A dermoscopy image of a single skin lesion.
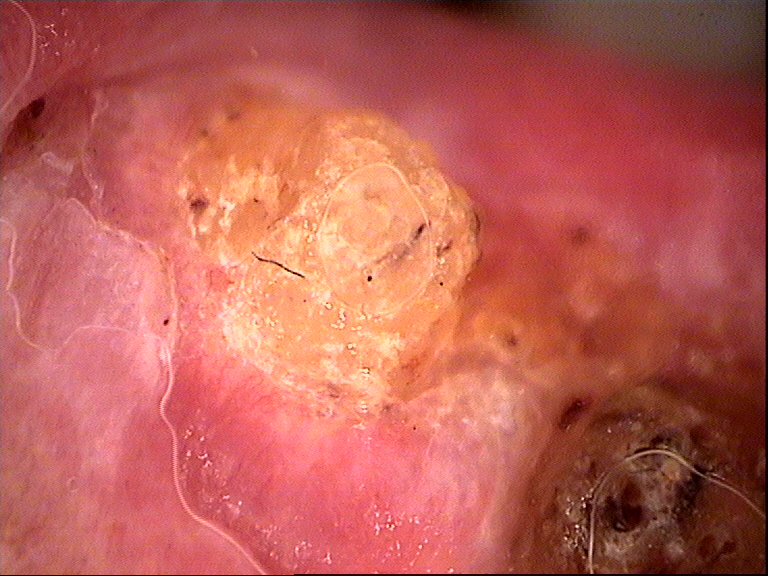Confirmed on histopathology as a keratinocytic lesion — a squamous cell carcinoma.